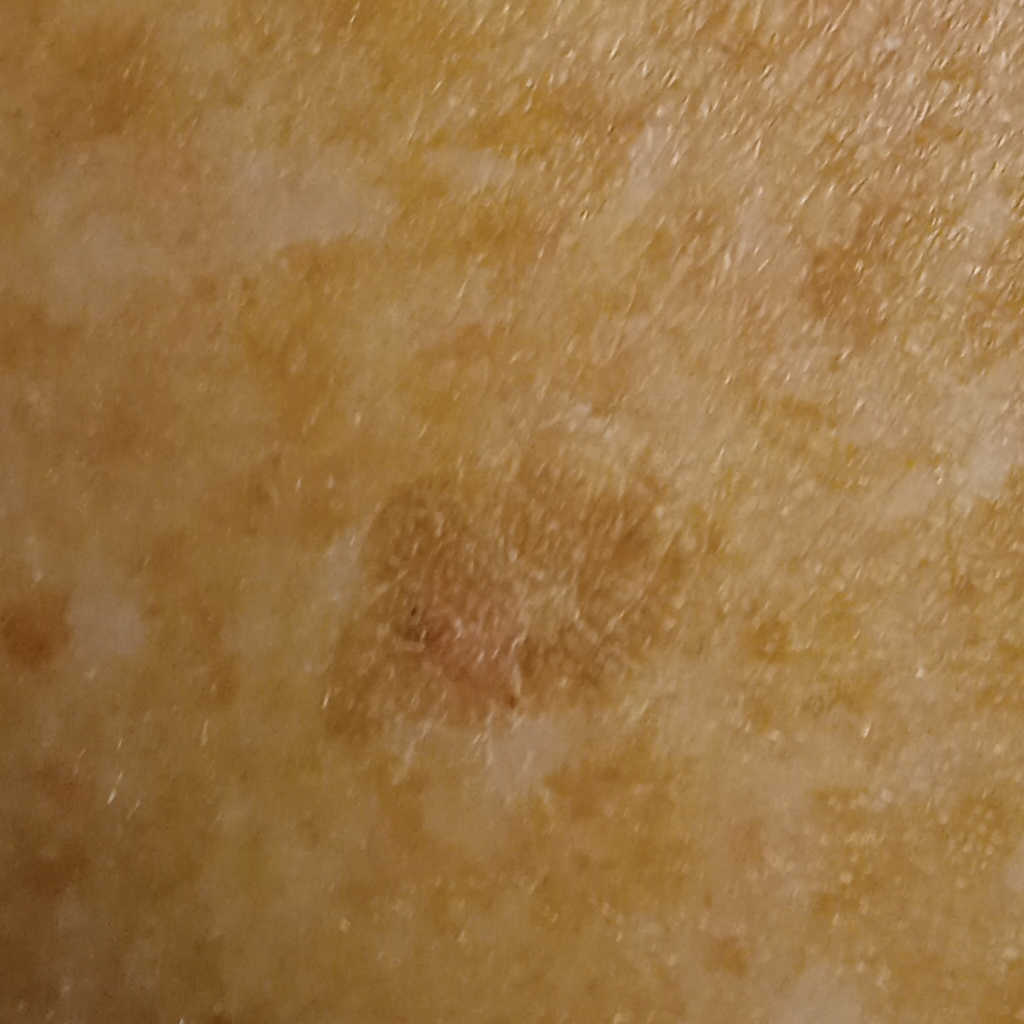{
  "image": "clinical photograph",
  "sun_reaction": "skin reddens with sun exposure",
  "diagnosis": {
    "name": "seborrheic keratosis",
    "malignancy": "benign"
  }
}